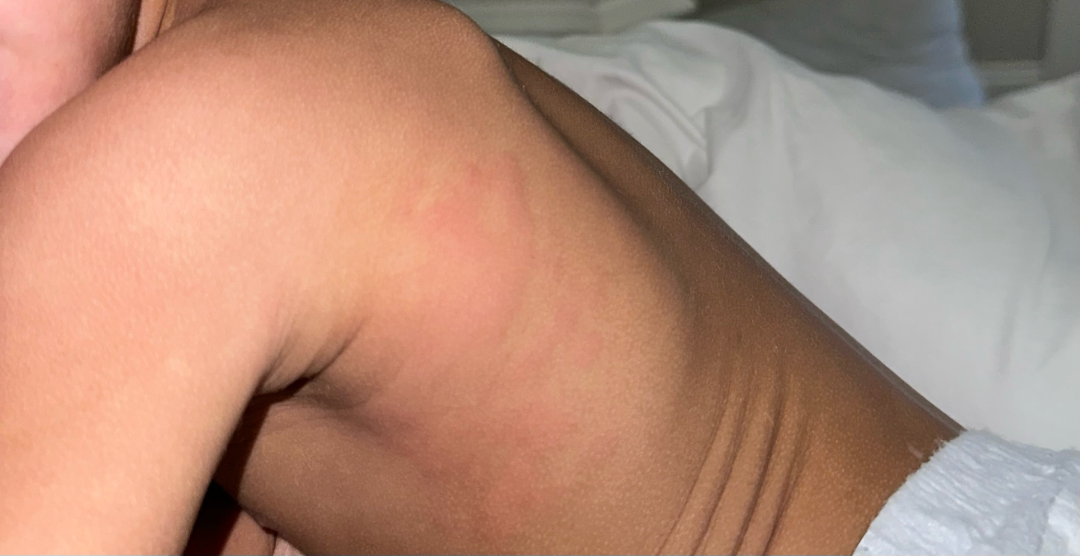Assessment:
The reviewing dermatologist's impression was: most likely Urticaria; possibly Allergic Contact Dermatitis.